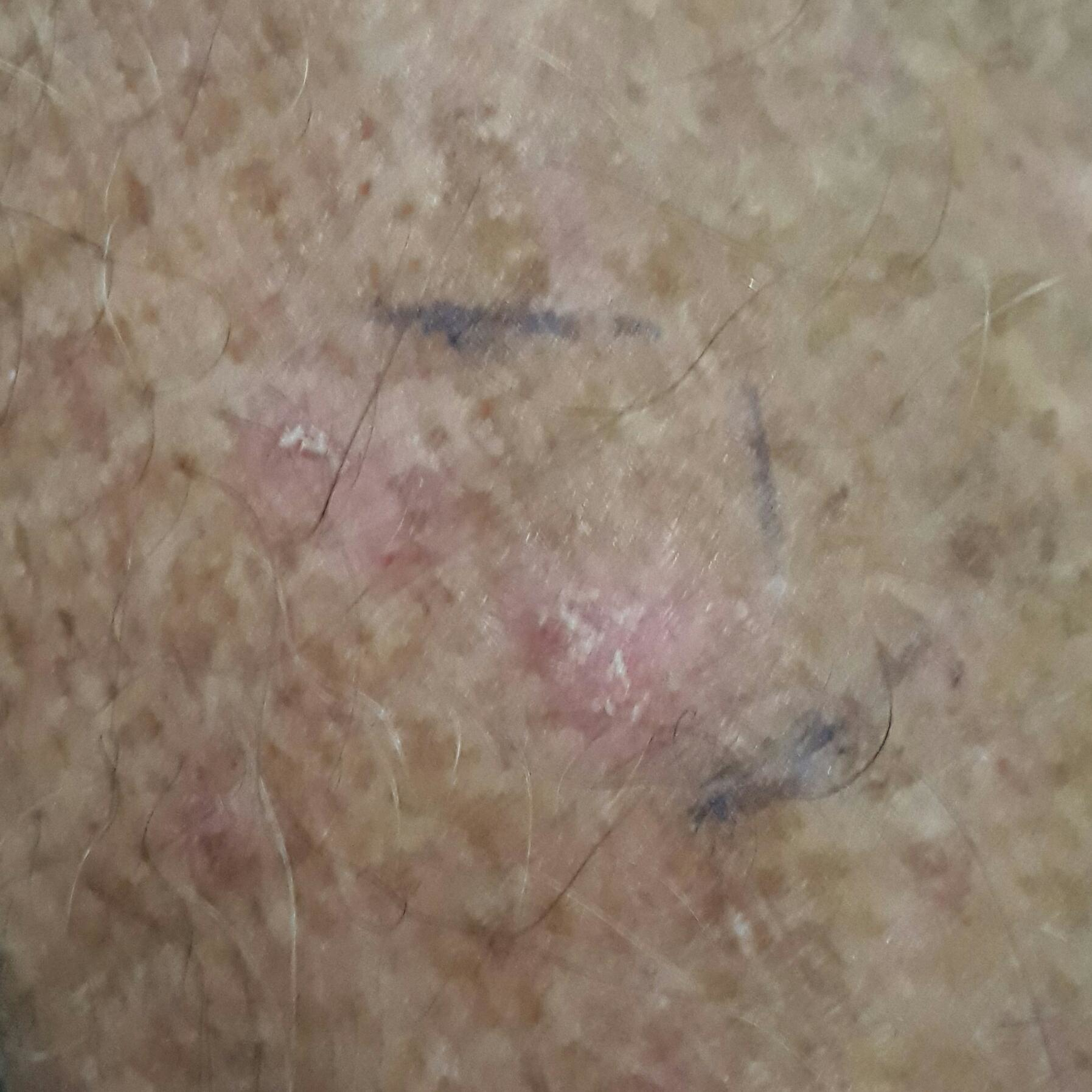Q: Patient demographics?
A: male, 70 years old
Q: Any relevant history?
A: pesticide exposure, no alcohol use, no tobacco use
Q: What is the imaging modality?
A: clinical photo
Q: Where on the body is the lesion?
A: a forearm
Q: Lesion size?
A: approx. 10 × 10 mm
Q: What does the patient describe?
A: itching
Q: What is the diagnosis?
A: actinic keratosis (clinical consensus)